The lesion involves the arm · reported duration is less than one week · lay reviewers estimated 5 on the Monk skin tone scale · the contributor reports the lesion is raised or bumpy · self-categorized by the patient as a rash · the lesion is associated with itching · a close-up photograph · the contributor is a female aged 50–59 — 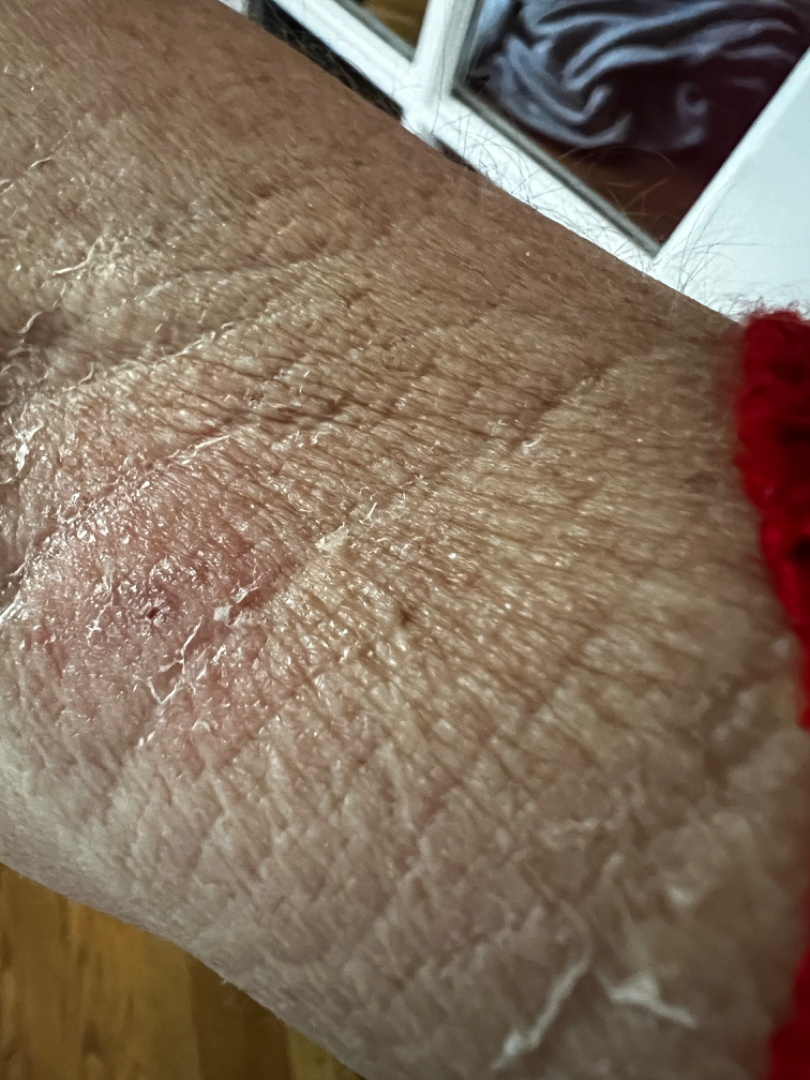Impression:
On remote review of the image, consistent with Lichenified eczema.